A skin lesion imaged with a dermatoscope:
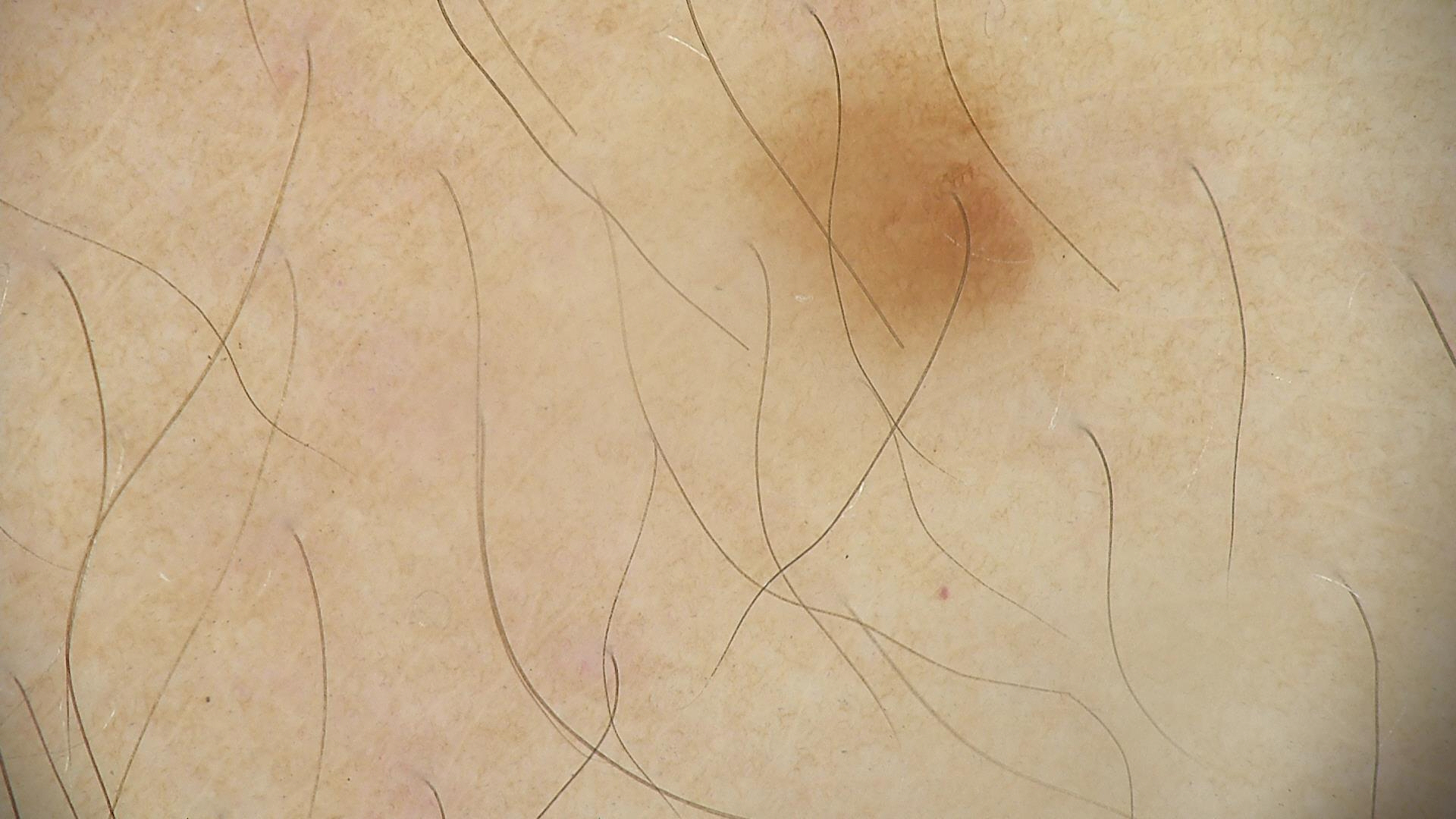{"diagnosis": {"name": "lentigo simplex", "code": "ls", "malignancy": "benign", "super_class": "melanocytic", "confirmation": "expert consensus"}}